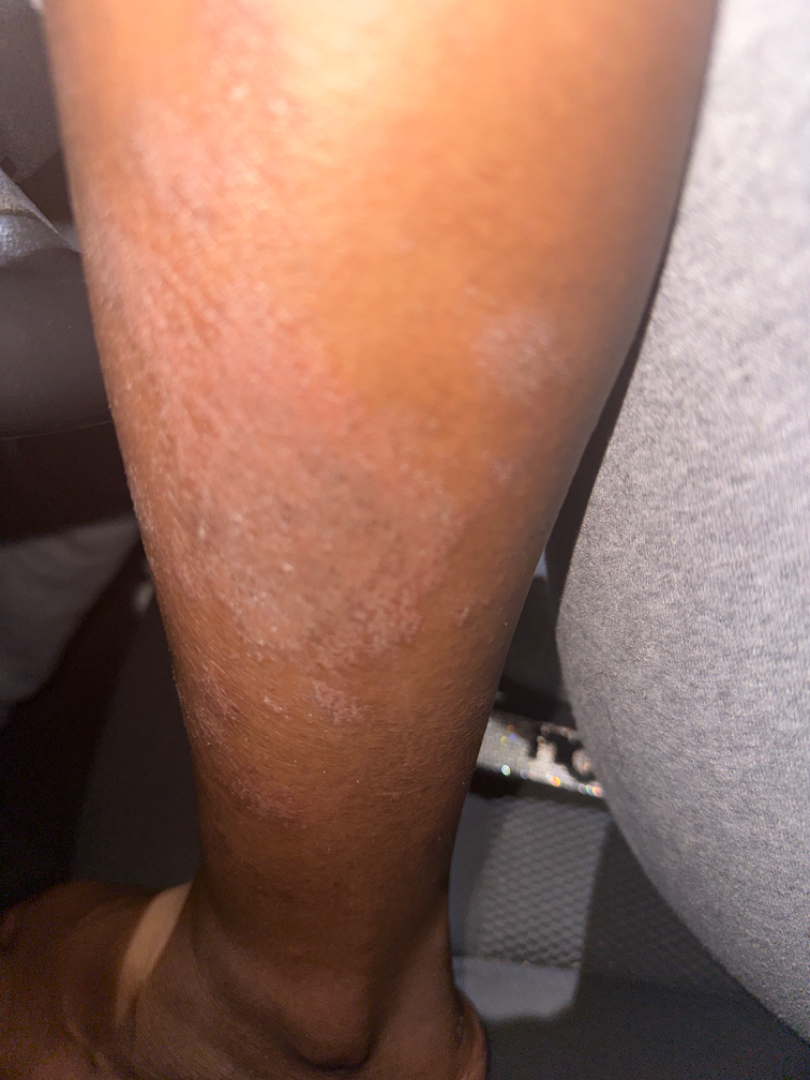| feature | finding |
|---|---|
| assessment | Psoriasis and Eczema were considered with similar weight; a remote consideration is Cutaneous T Cell Lymphoma |